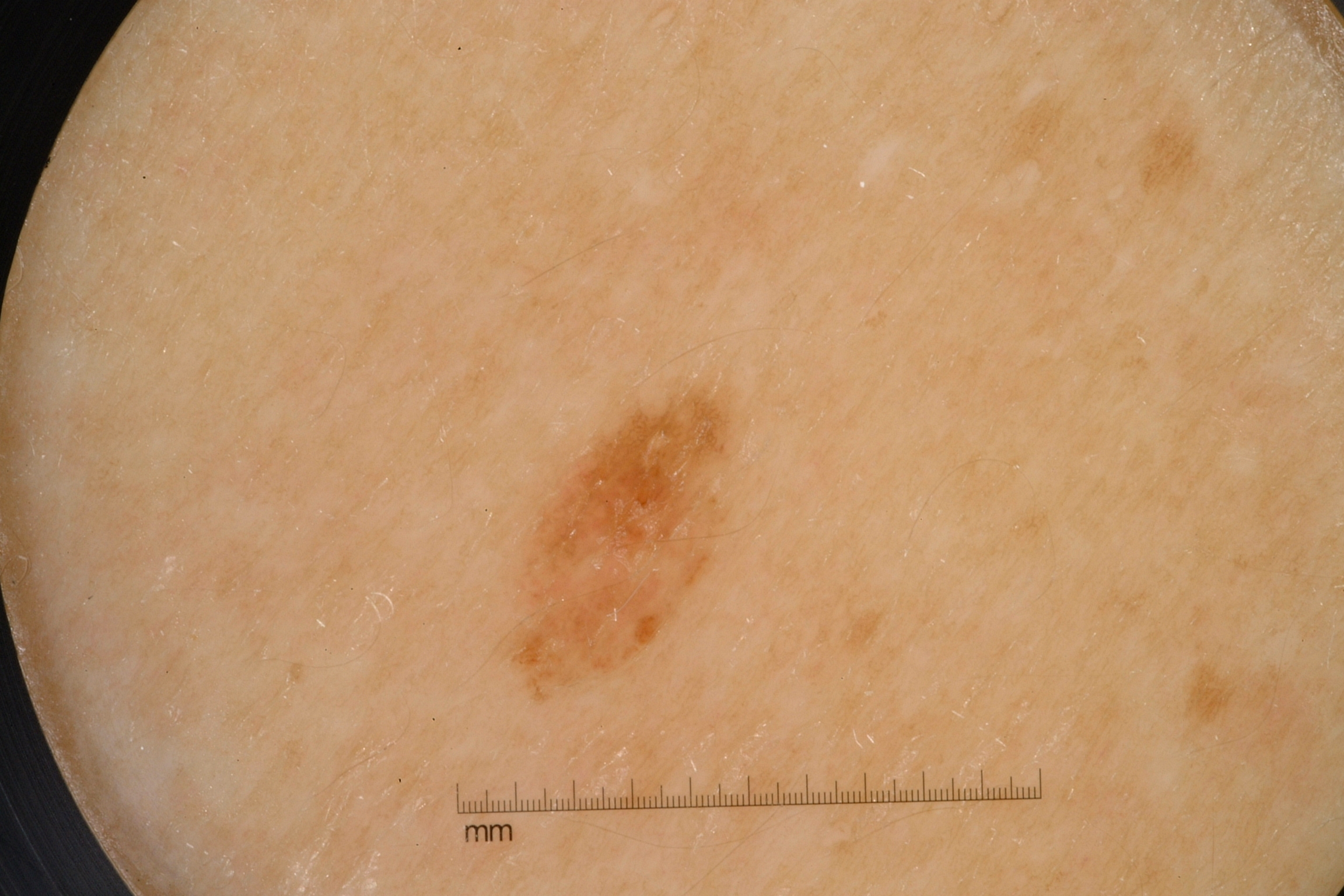modality — dermoscopy of a skin lesion
dermoscopic features — pigment network; absent: negative network, streaks, and milia-like cysts
lesion bbox — [488, 373, 751, 706]
impression — a melanocytic nevus, a benign lesion